Close-up view: 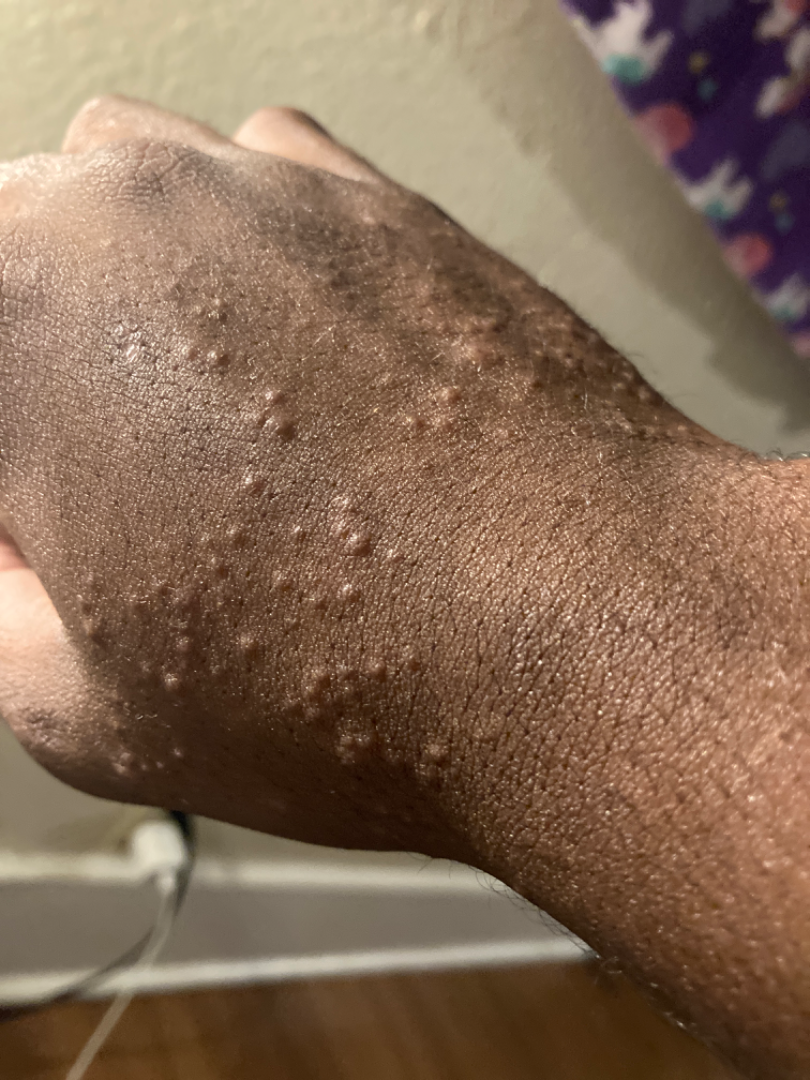Q: Could the case be diagnosed?
A: not assessable